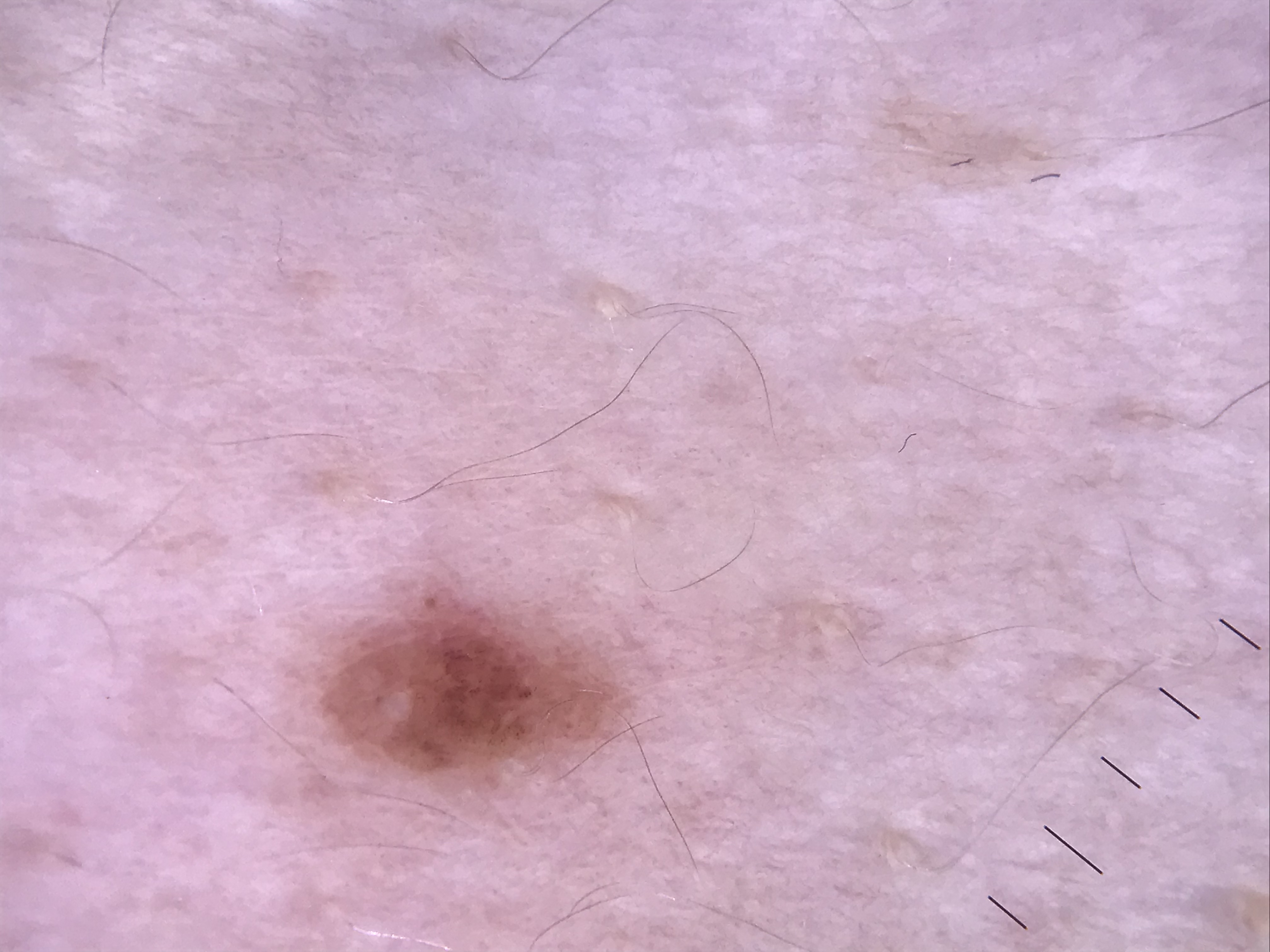The diagnostic label was a compound nevus.